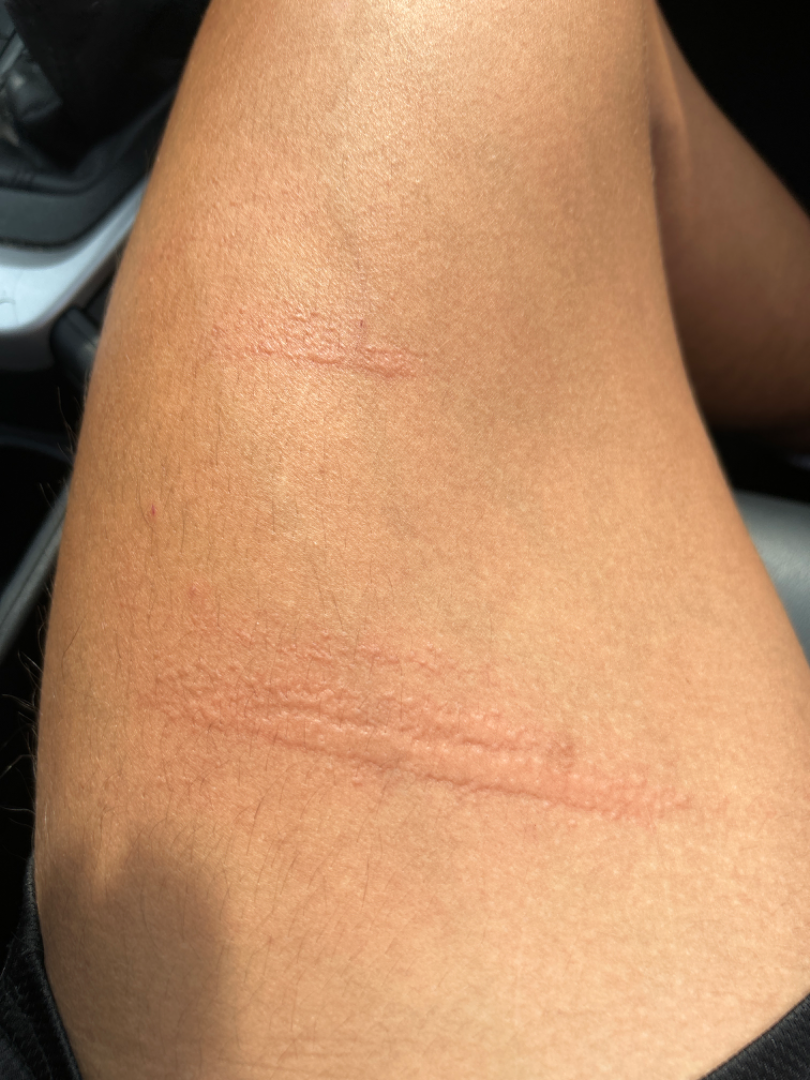History: Present for about one day. Close-up view. The lesion involves the leg. The contributor notes the lesion is raised or bumpy. Impression: Consistent with Allergic Contact Dermatitis.